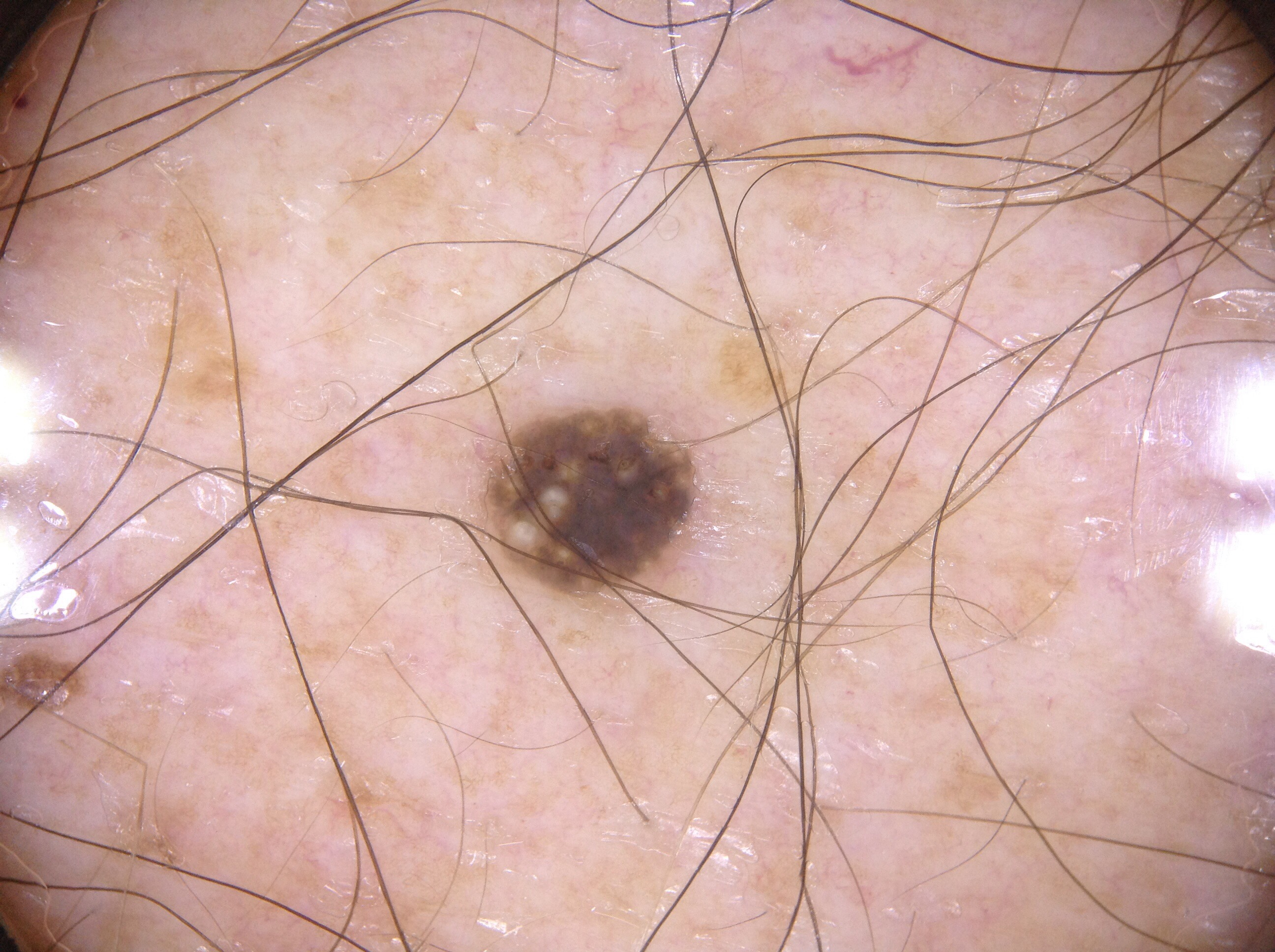image — dermoscopy | subject — male, aged 73 to 77 | dermoscopic findings — milia-like cysts | lesion bbox — [488, 409, 697, 595] | assessment — a seborrheic keratosis, a benign skin lesion.